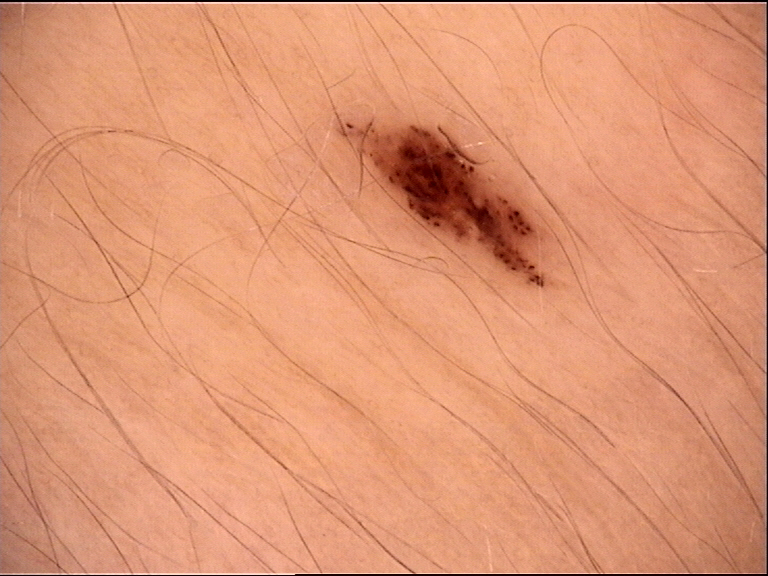assessment: dysplastic junctional nevus (expert consensus)